A clinical photograph showing a skin lesion; a male patient in their 80s — 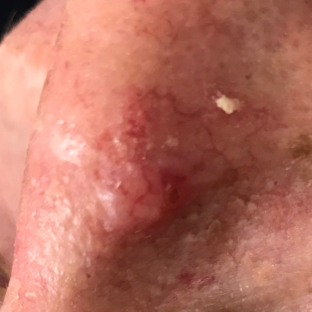  lesion_location: the nose
  symptoms:
    present:
      - elevation
      - itching
  diagnosis:
    name: basal cell carcinoma
    code: BCC
    malignancy: malignant
    confirmation: histopathology